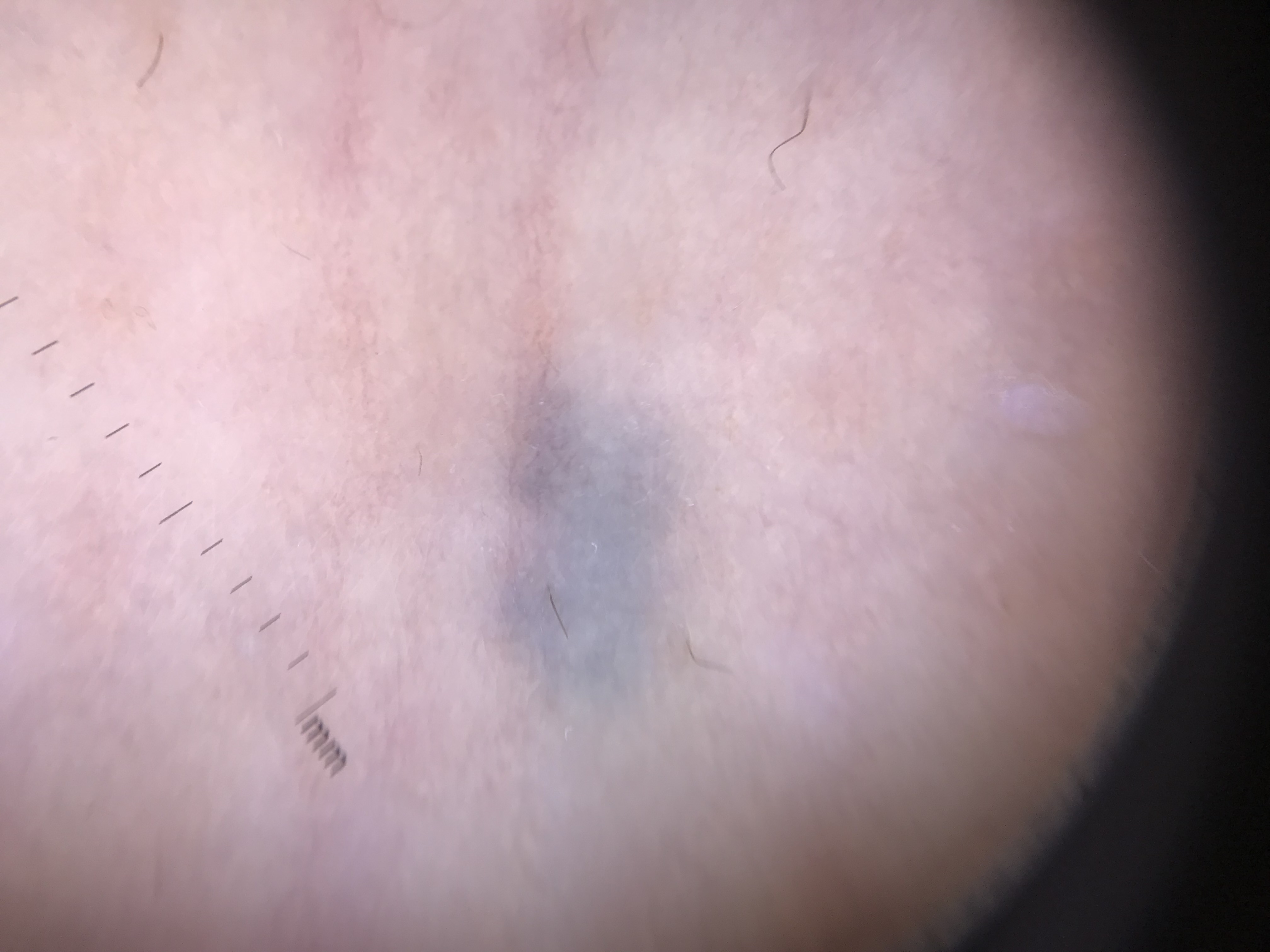classification = banal, dermal | assessment = blue nevus (expert consensus).